This image was taken at an angle · the patient is a female aged 30–39 · self-categorized by the patient as a rash · the affected area is the leg and arm · reported duration is one to four weeks — 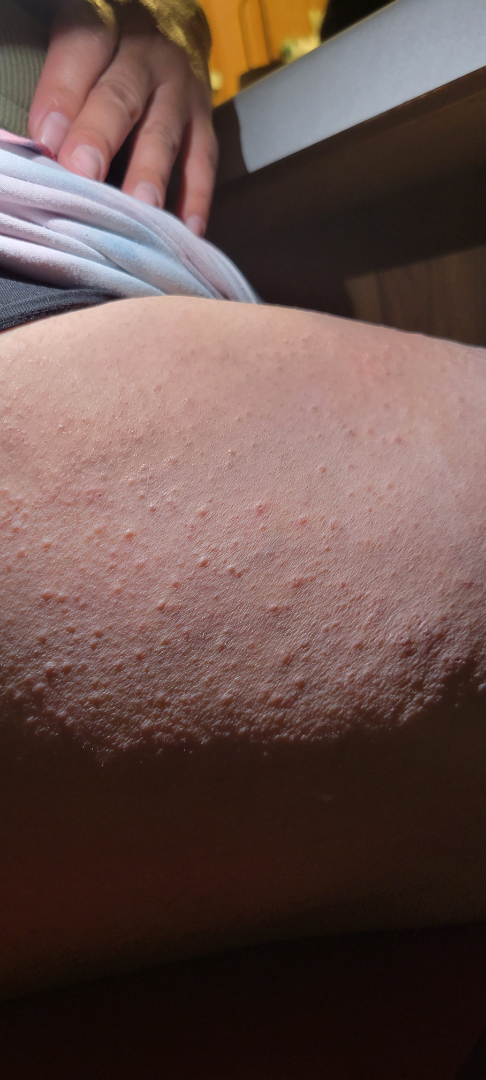dermatologist impression = three dermatologists each reviewed the case: the differential, in no particular order, includes Keratosis pilaris and Eczema